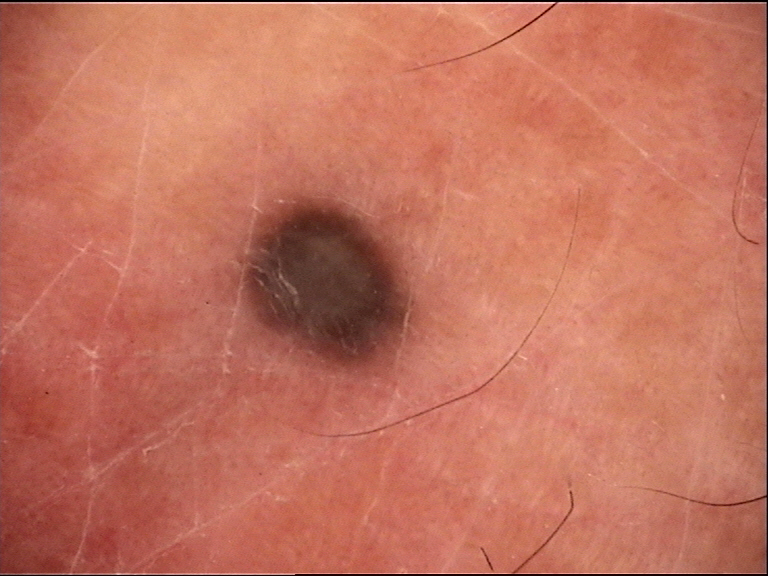A dermoscopic photograph of a skin lesion. Diagnosed as a blue nevus.